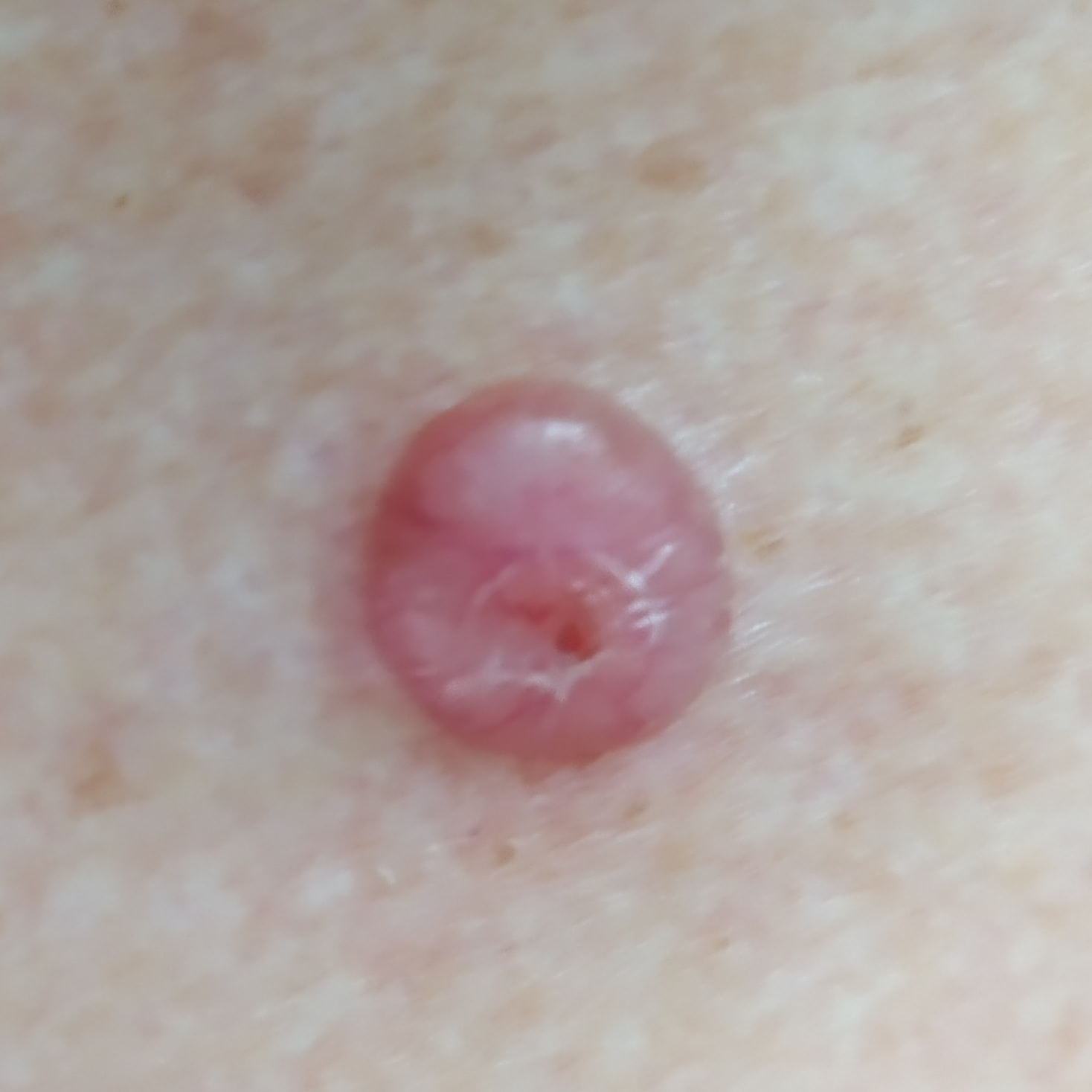| key | value |
|---|---|
| patient | female, aged 75 |
| image type | smartphone clinical photo |
| skin type | II |
| body site | the back |
| diameter | 10x10 mm |
| reported symptoms | growth, bleeding, elevation, itching |
| diagnostic label | basal cell carcinoma (biopsy-proven) |